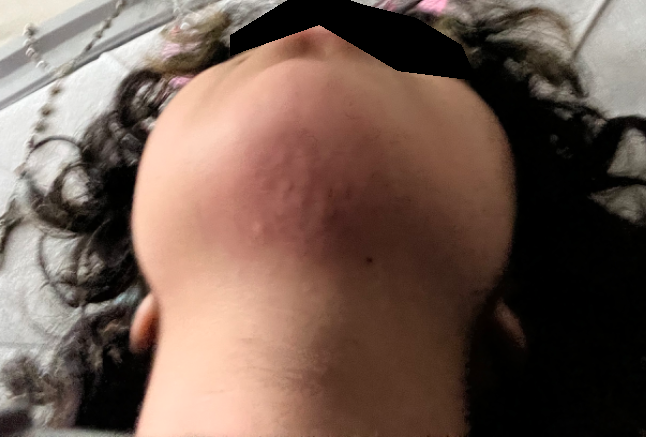constitutional symptoms = none reported | site = head or neck | patient's own categorization = a rash | symptoms = pain, bothersome appearance, bleeding, burning and itching | shot type = at a distance | differential diagnosis = most consistent with Impetigo; with consideration of Folliculitis.